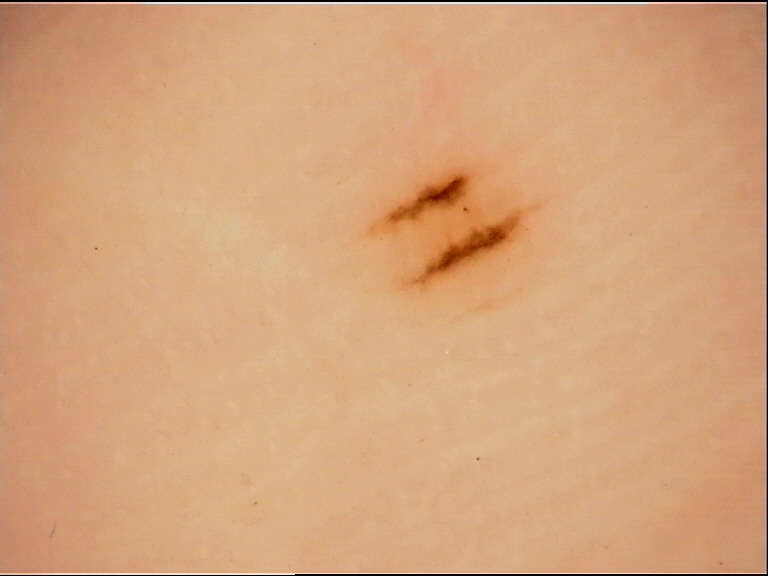Case:
– class · acral junctional nevus (expert consensus)